A dermoscopic close-up of a skin lesion: 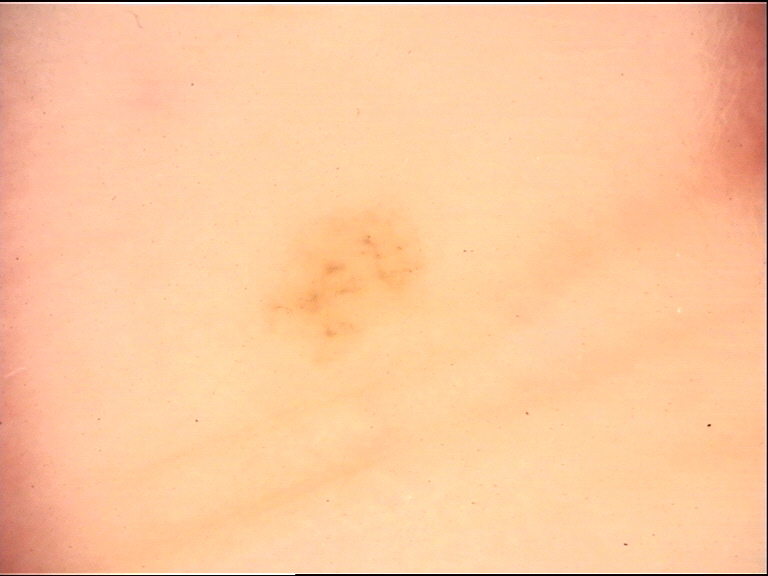The diagnostic label was an acral dysplastic junctional nevus.